Close-up view; the patient is 30–39, female — 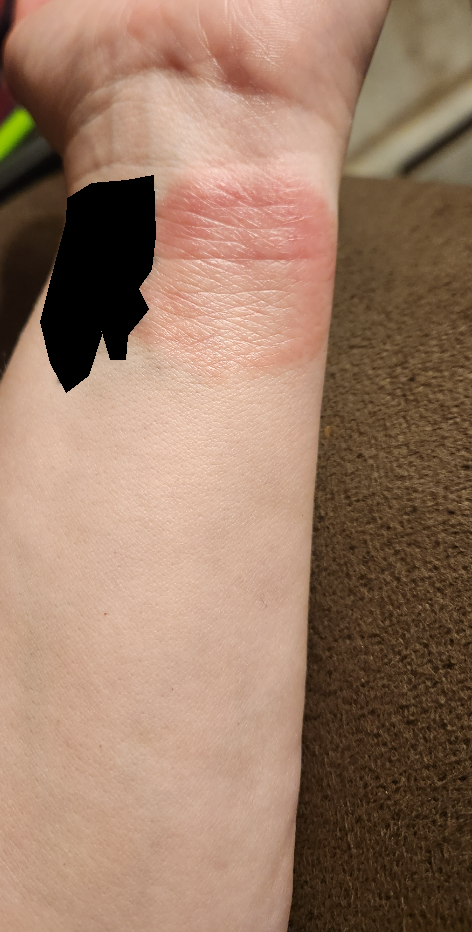Chronic dermatitis, NOS (considered); Allergic Contact Dermatitis (considered).